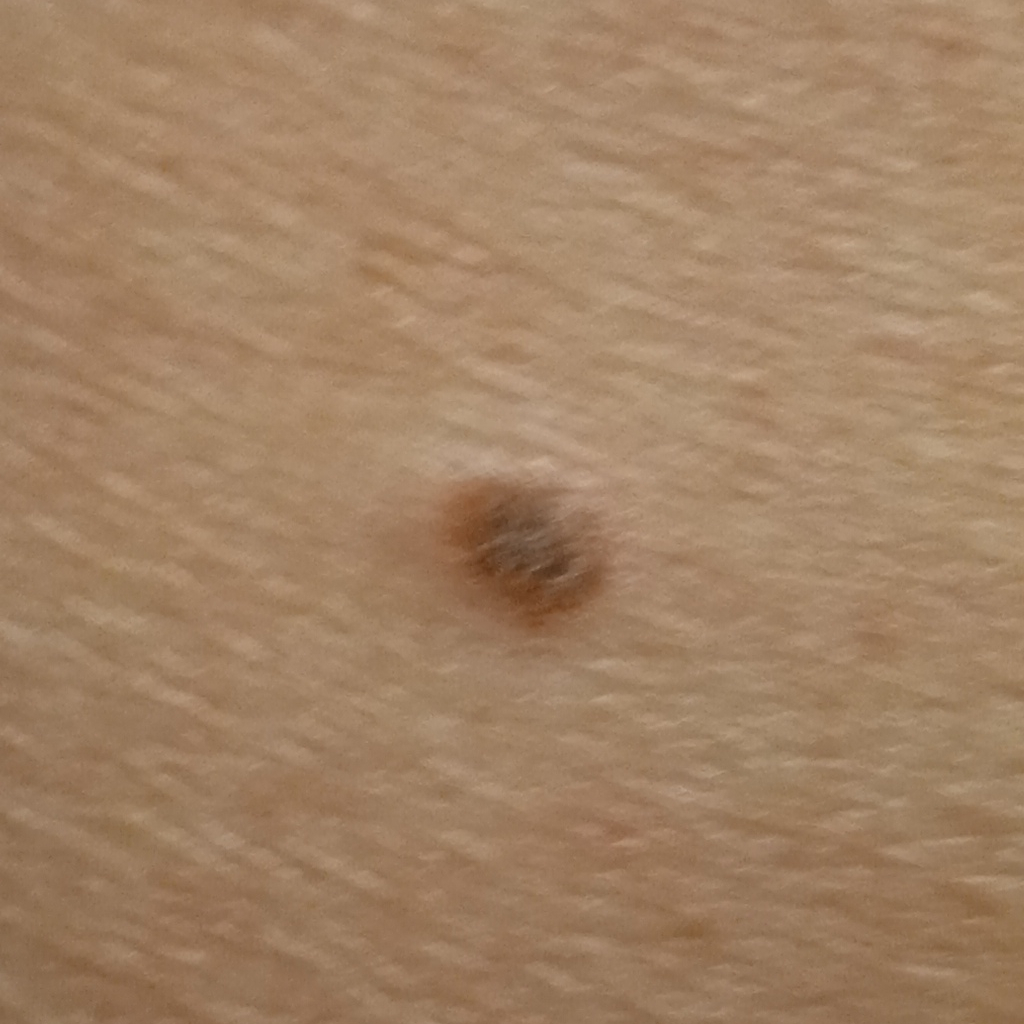sun reaction: skin tans without first burning
patient: male, age 79
clinical context: research study (no referral diagnosis)
size: 5.9 mm
assessment: seborrheic keratosis (dermatologist consensus)